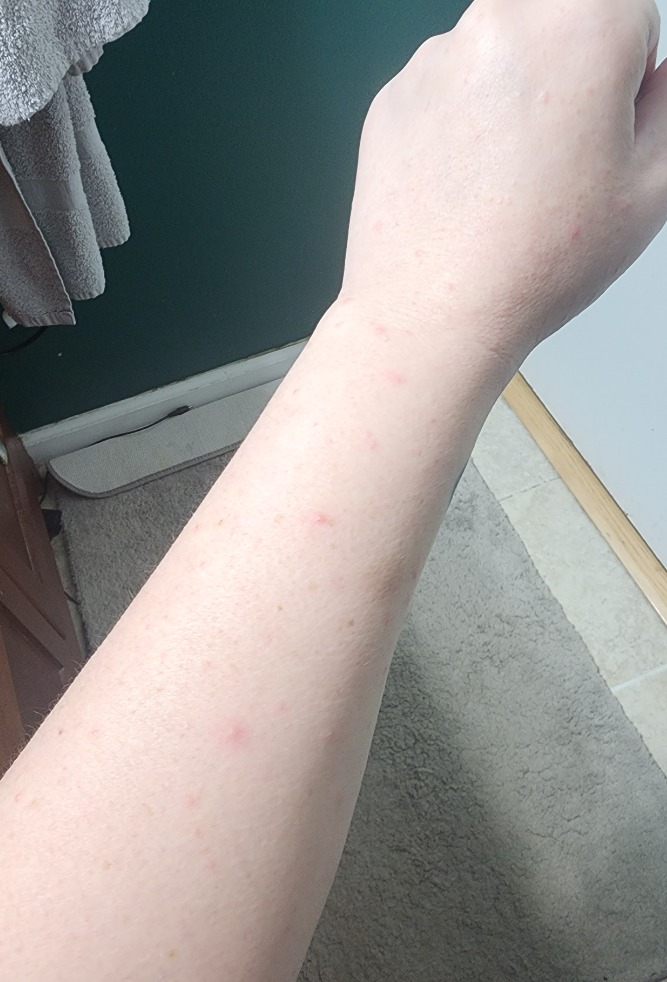impression: Folliculitis (0.67); Insect Bite (0.33).